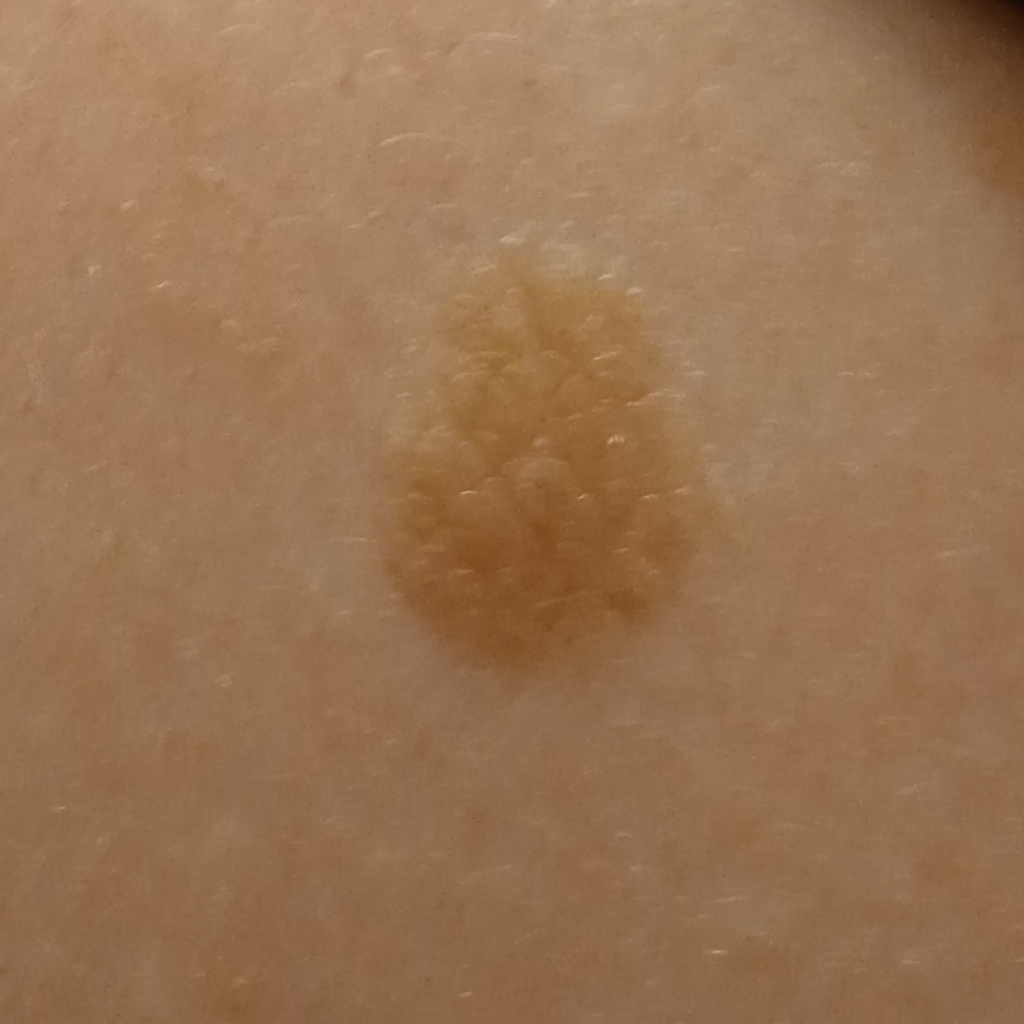Acquired for a research image collection, with no referral diagnosis. A female patient 39 years of age. A clinical photograph of a skin lesion. The patient says their skin reddens with sun exposure. The patient describes having few moles overall. Measuring roughly 10.1 mm. The diagnostic impression was a seborrheic keratosis.